The subject is a female aged approximately 70. A dermoscopic close-up of a skin lesion — 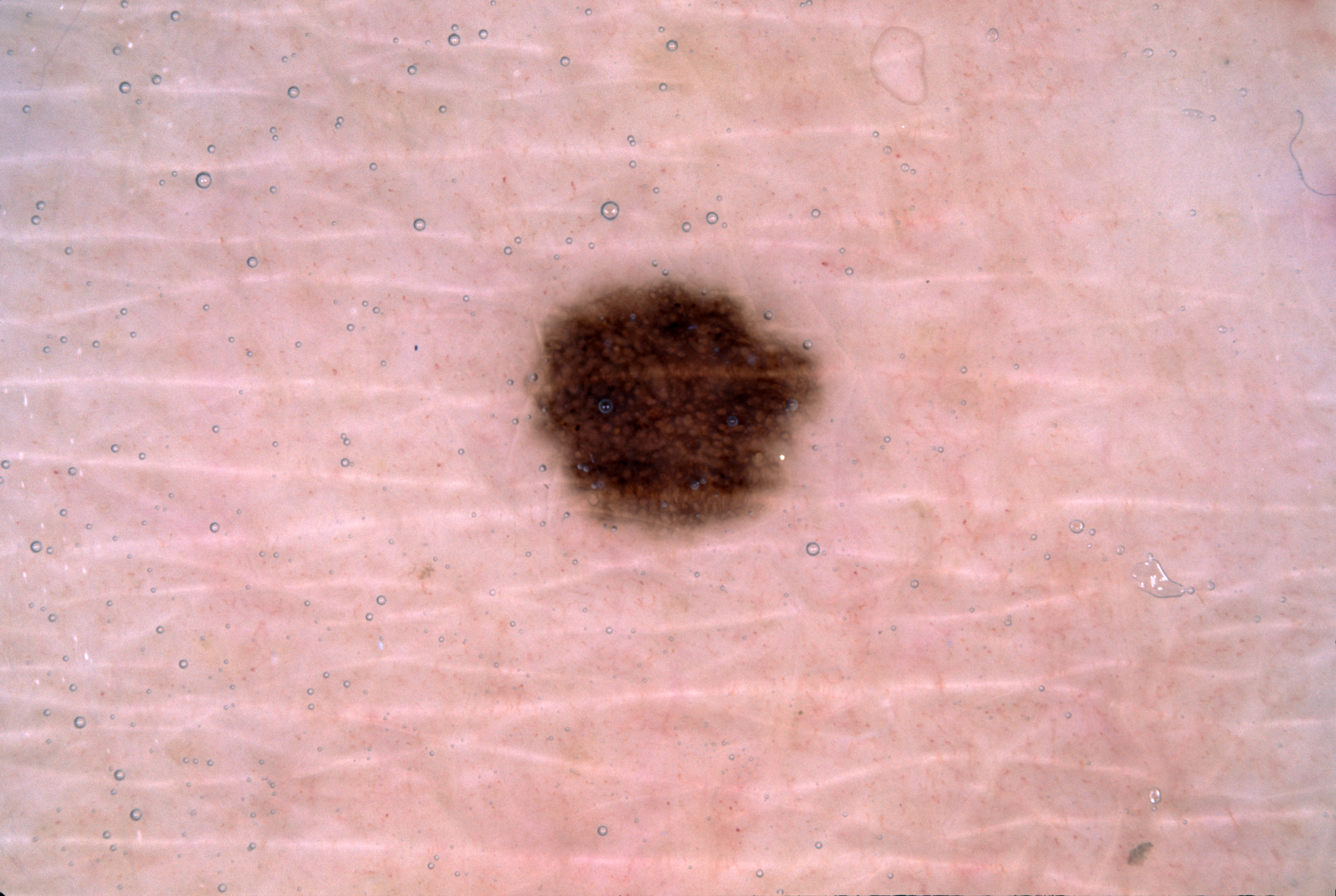Q: Where is the lesion located?
A: [523, 273, 824, 537]
Q: What dermoscopic features are present?
A: pigment network; absent: negative network, milia-like cysts, and streaks
Q: What is this lesion?
A: a melanocytic nevus